Present for about one day. The head or neck, arm, palm and front of the torso are involved. Close-up view. Self-categorized by the patient as a rash. Male contributor, age 18–29: 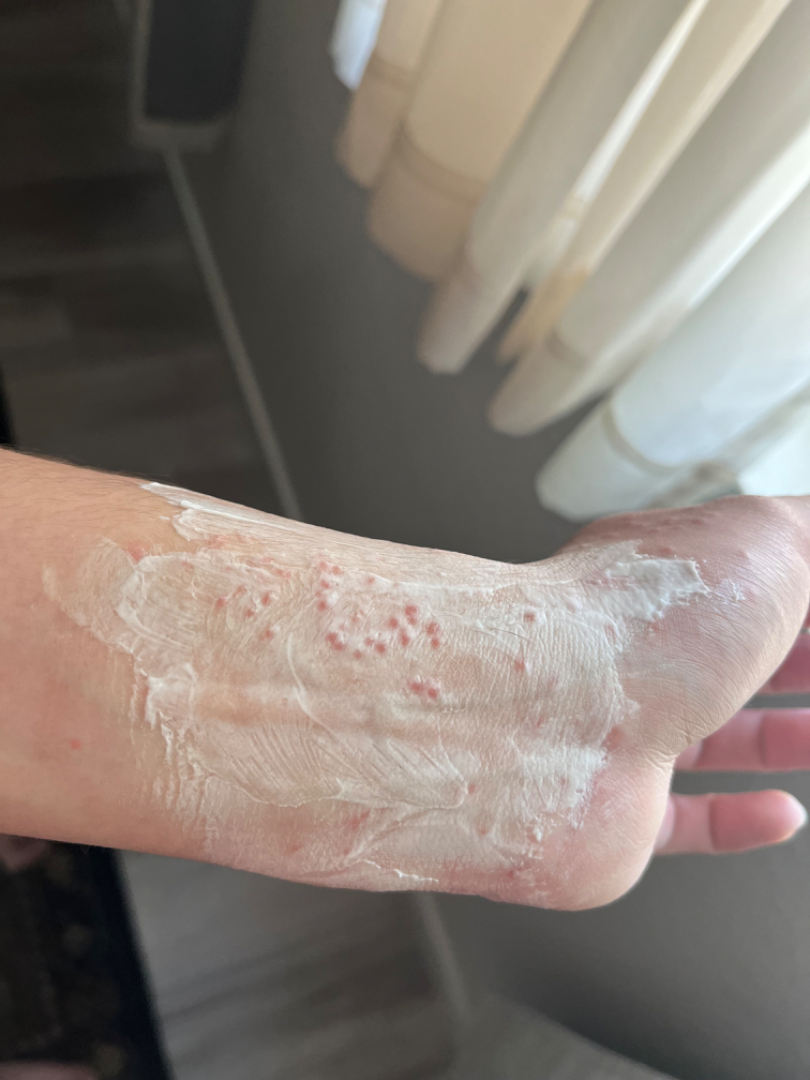A single dermatologist reviewed the case: the differential is split between Insect Bite and Allergic Contact Dermatitis.